A dermoscopic image of a skin lesion.
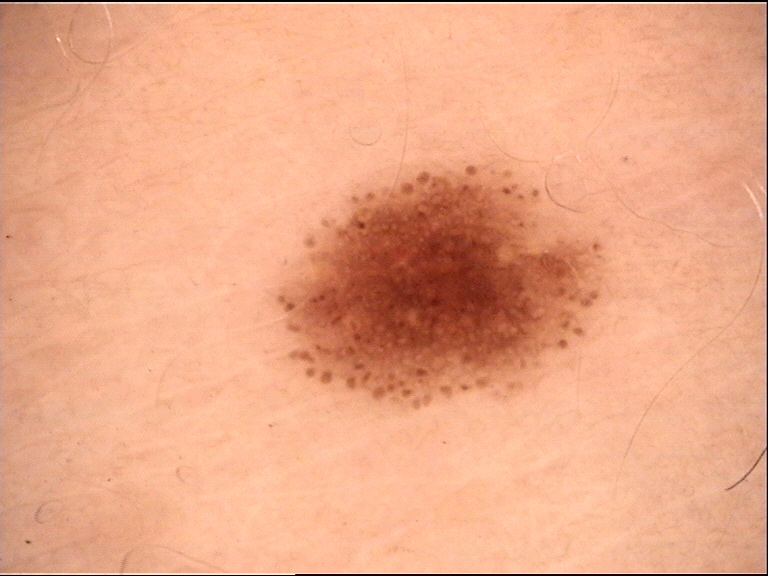Consistent with a benign lesion — a dysplastic junctional nevus.